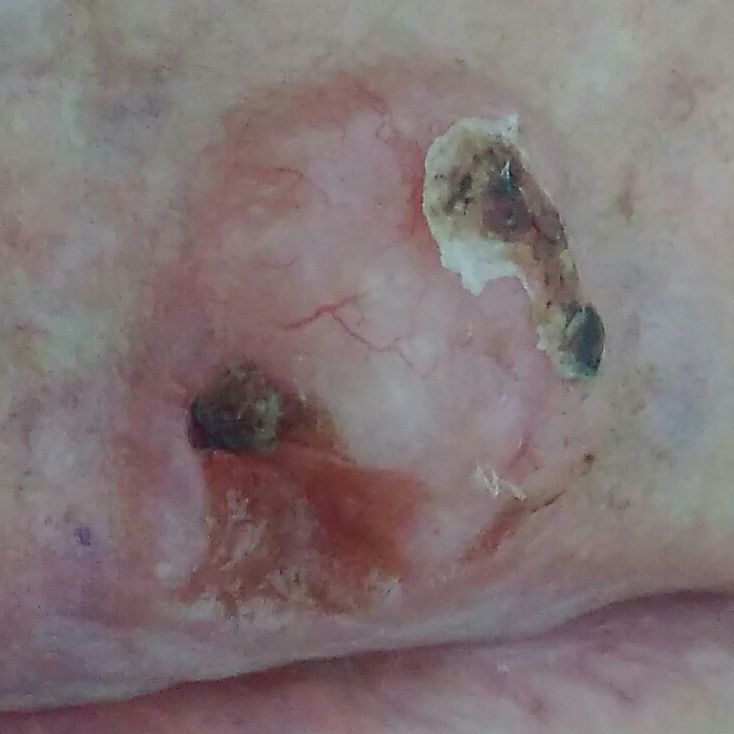A female subject 73 years of age.
History notes prior skin cancer (patient or family) and no prior malignancy (patient or family).
The lesion is on a lip.
Measuring about 18 × 16 mm.
By the patient's account, the lesion itches, has bled, is elevated, and hurts.
The biopsy diagnosis was a malignancy — a basal cell carcinoma.